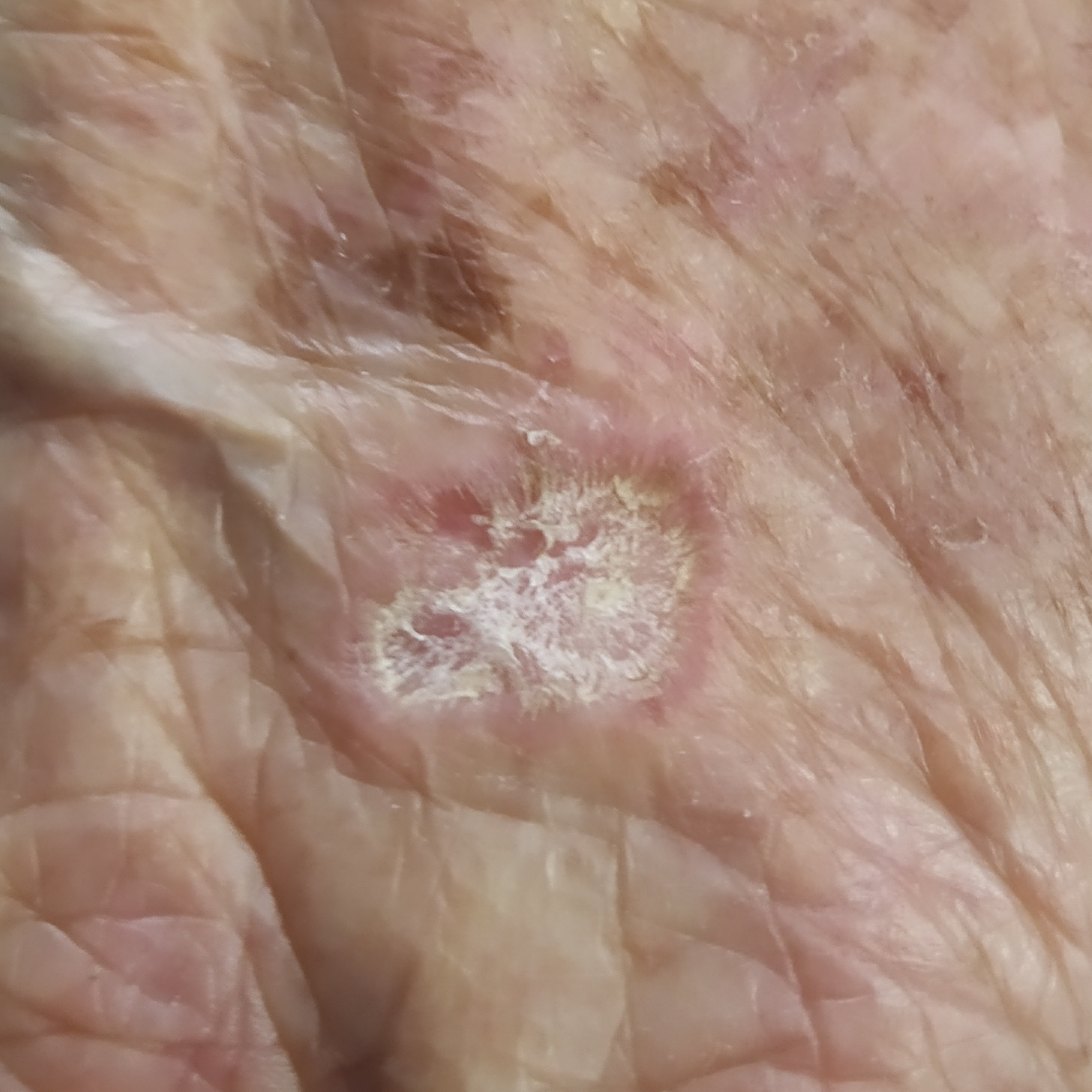Diagnosis: Histopathologically confirmed as an actinic keratosis.